Reported duration is about one day. The patient reports bothersome appearance. The patient considered this a pigmentary problem. Skin tone: Fitzpatrick IV. No relevant systemic symptoms. The patient reports the lesion is flat. The photograph was taken at an angle: 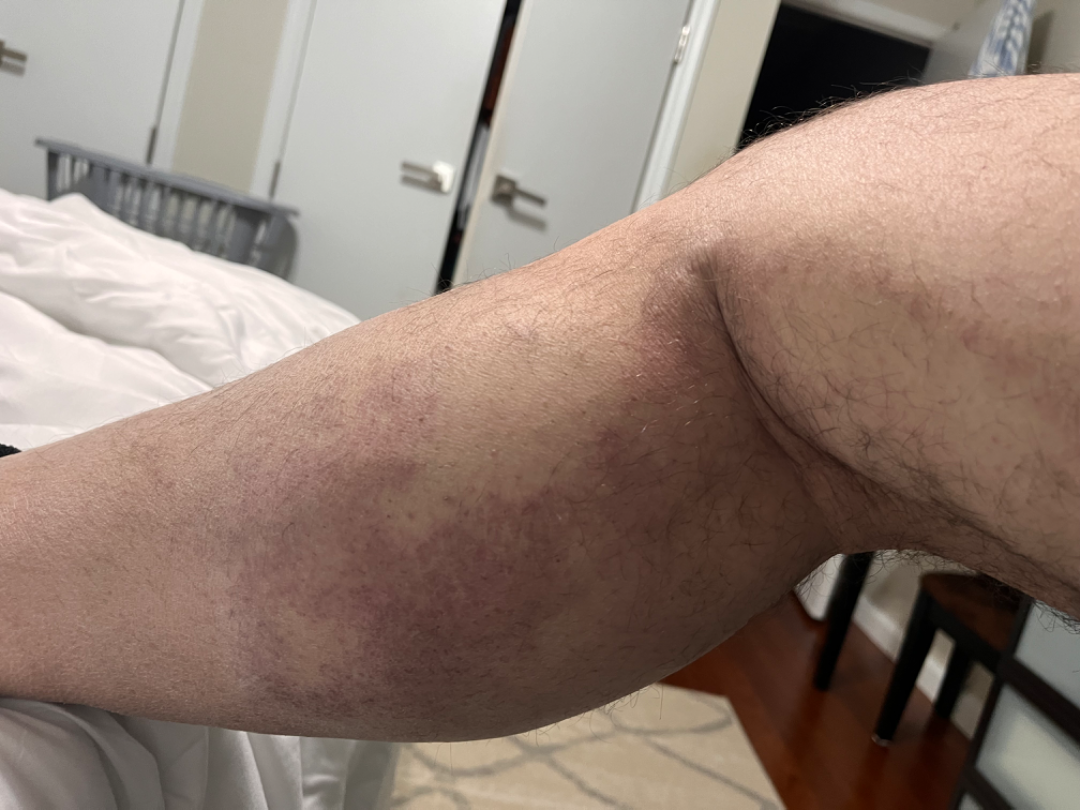{"differential": {"tied_lead": ["Pigmented purpuric eruption", "ecchymoses", "Lichen planus/lichenoid eruption"]}}